The photograph was taken at a distance. The lesion involves the front of the torso, back of the torso, top or side of the foot, leg, arm, back of the hand and head or neck.
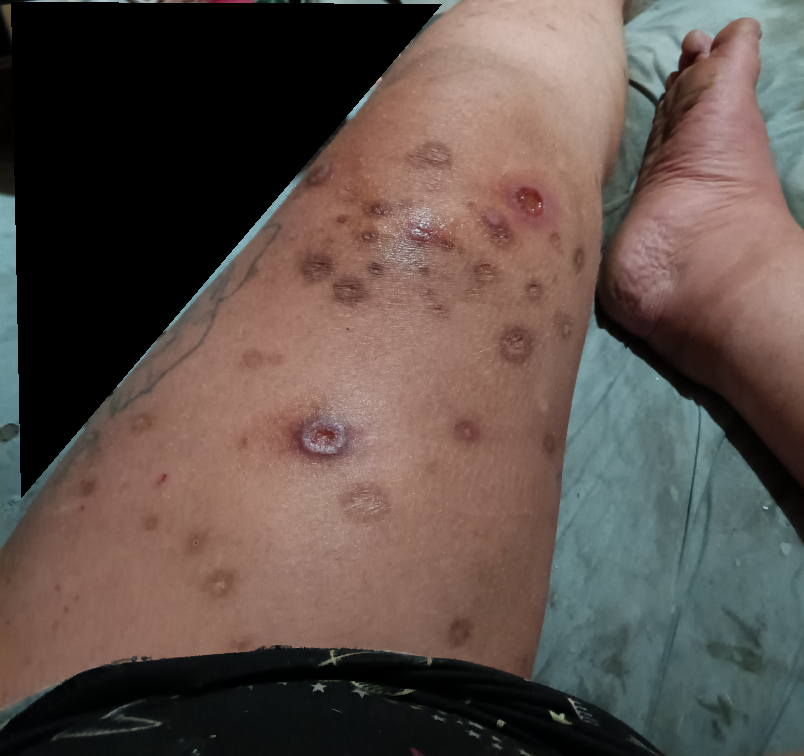dermatologist impression: most likely Skin lesion in drug addict; the differential also includes Ecthyma; a more distant consideration is Acute ulcer of skin.